A dermoscopic close-up of a skin lesion.
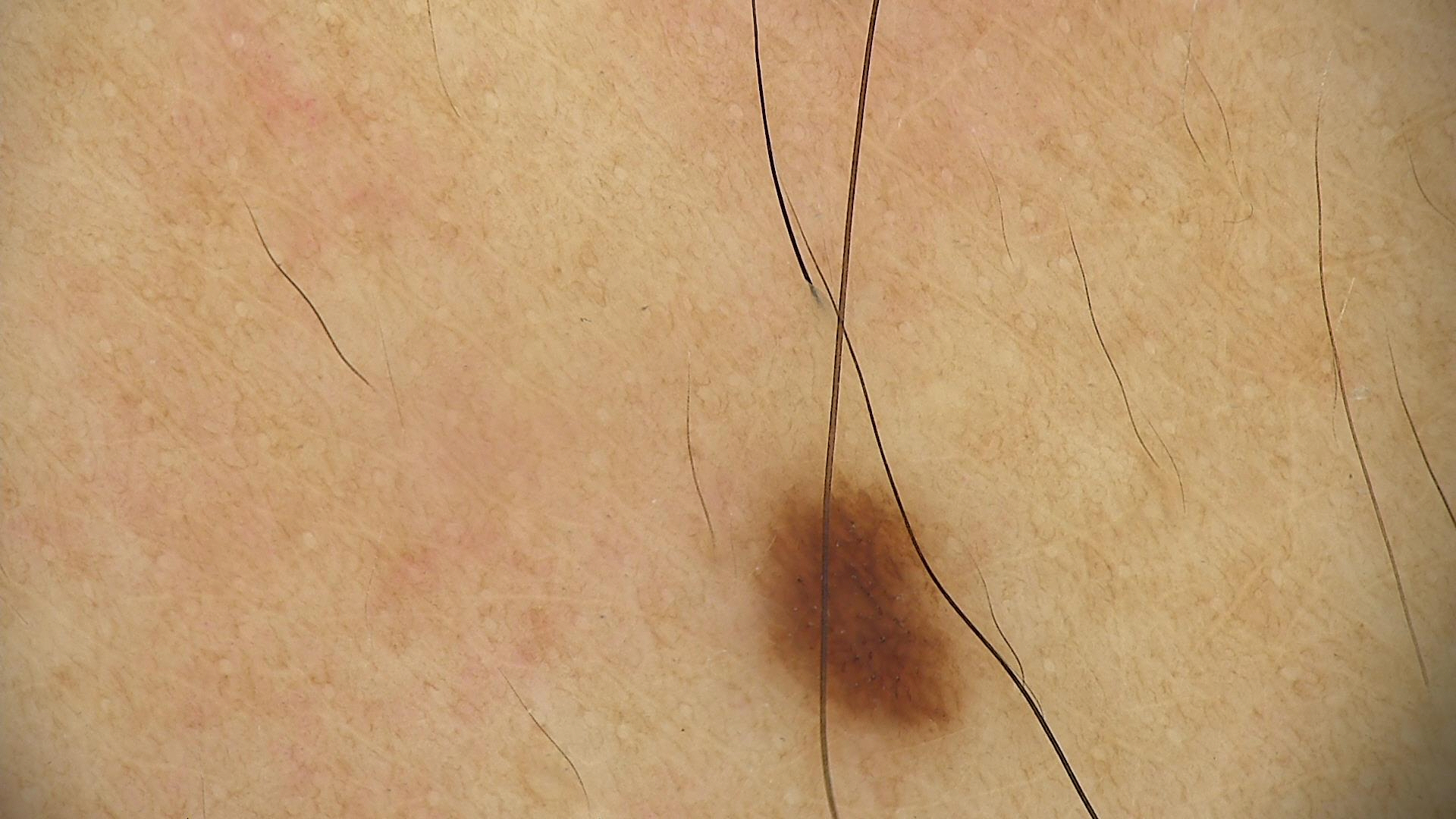Findings: The architecture is that of a banal lesion. Impression: Consistent with a junctional nevus.